A dermoscopy image of a single skin lesion:
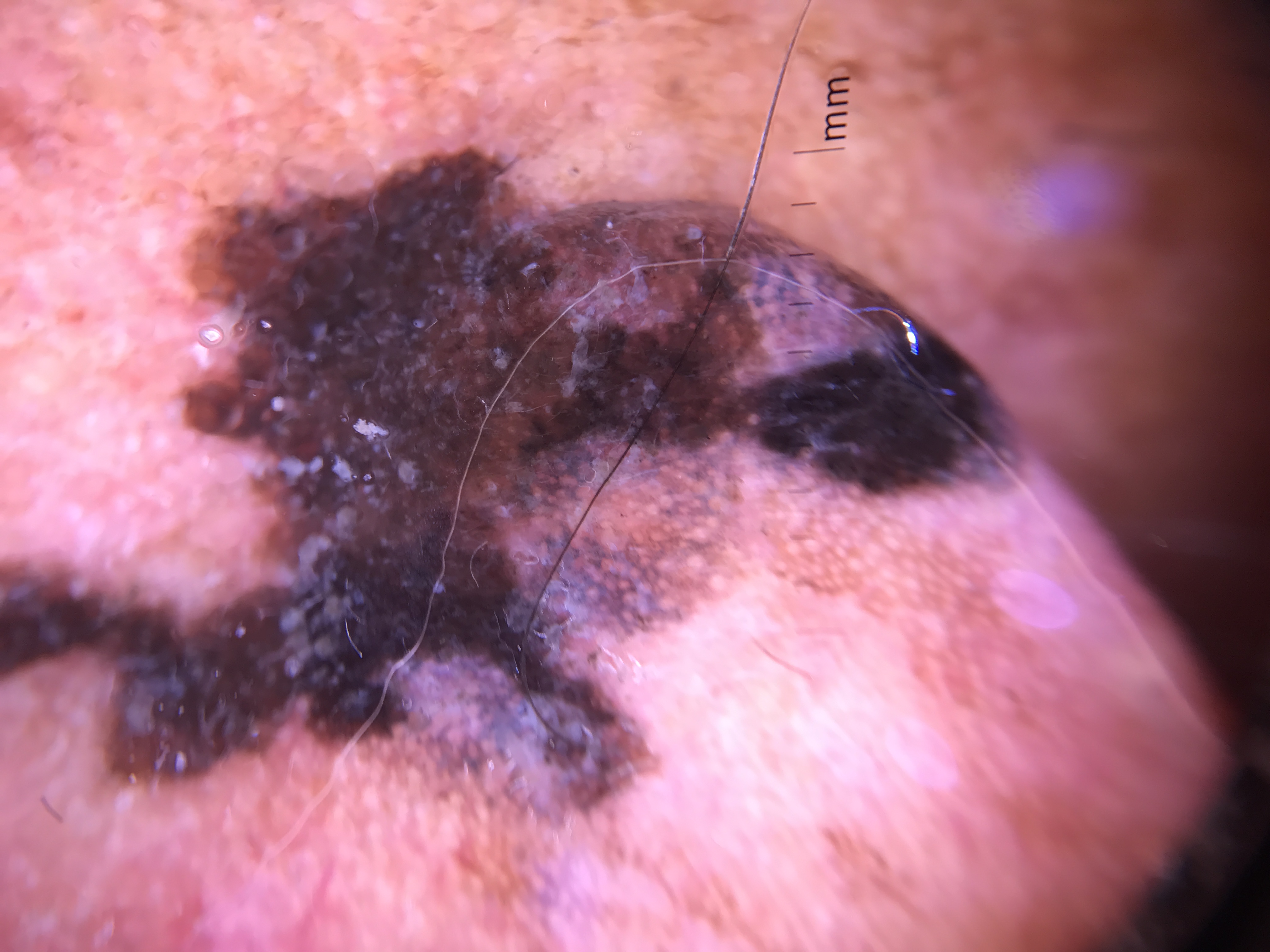{"diagnosis": {"name": "lentigo maligna", "code": "lm", "malignancy": "malignant", "super_class": "melanocytic", "confirmation": "histopathology"}}